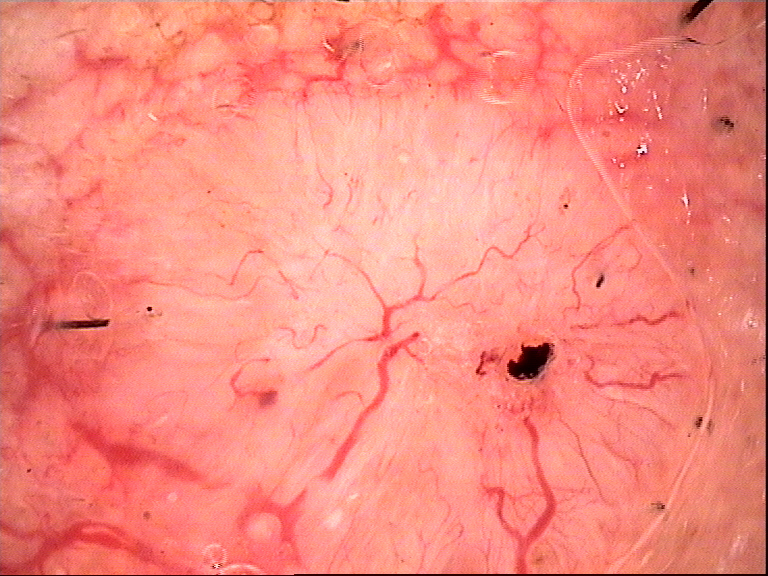Case:
• class: basal cell carcinoma (biopsy-proven)